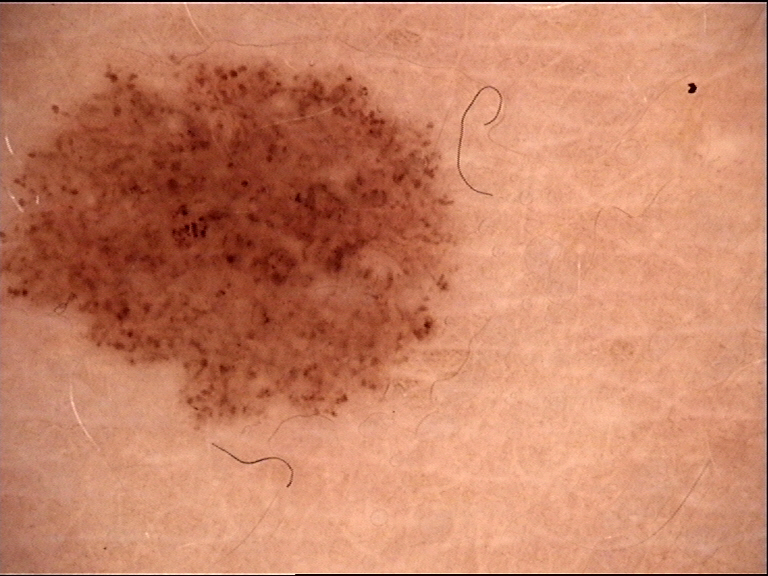Classified as a dysplastic junctional nevus.